A female patient age 26 · a dermoscopy image of a skin lesion · imaged for a research study, with no referral diagnosis recorded:
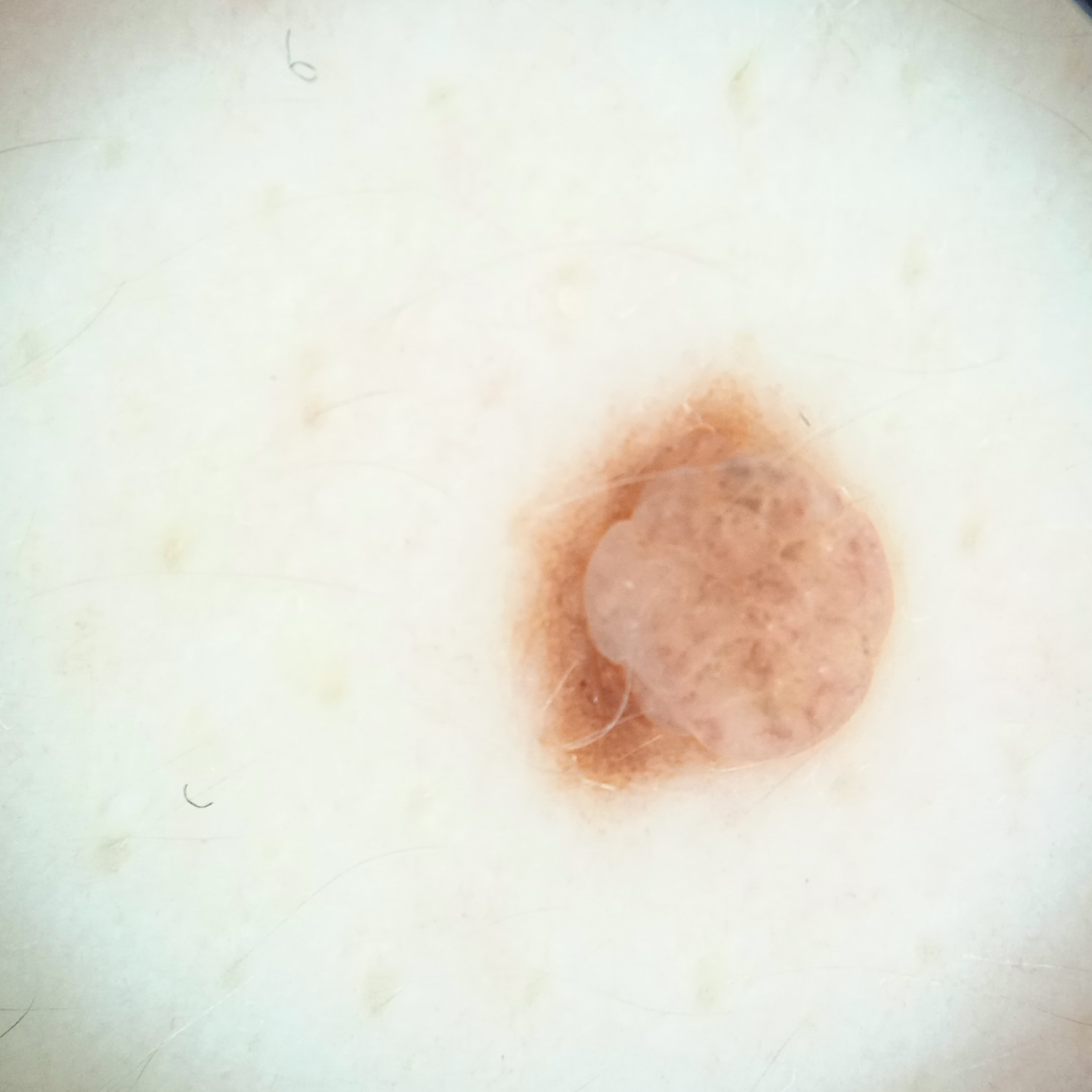Findings:
• body site: the back
• size: 4.5 mm
• diagnosis: melanocytic nevus (dermatologist consensus)